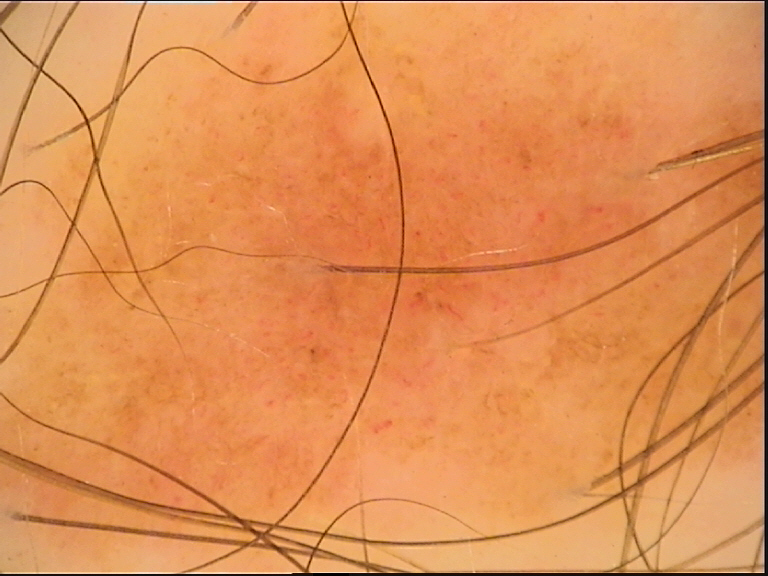Findings:
A dermoscopic close-up of a skin lesion.
Impression:
Diagnosed as a benign lesion — a dysplastic junctional nevus.